A skin lesion imaged with a dermatoscope.
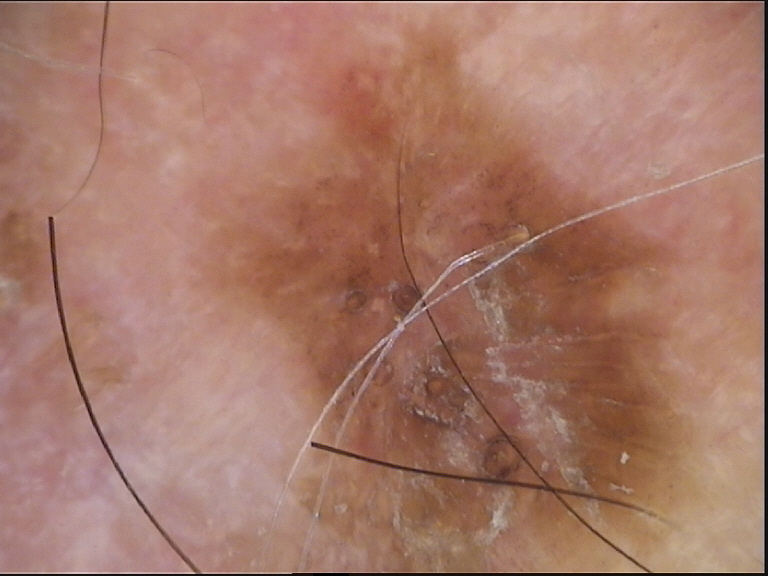<case>
<diagnosis>
<name>lichenoid keratosis</name>
<code>lk</code>
<malignancy>benign</malignancy>
<super_class>non-melanocytic</super_class>
<confirmation>expert consensus</confirmation>
</diagnosis>
</case>